The affected area is the leg, close-up view, the subject is female: 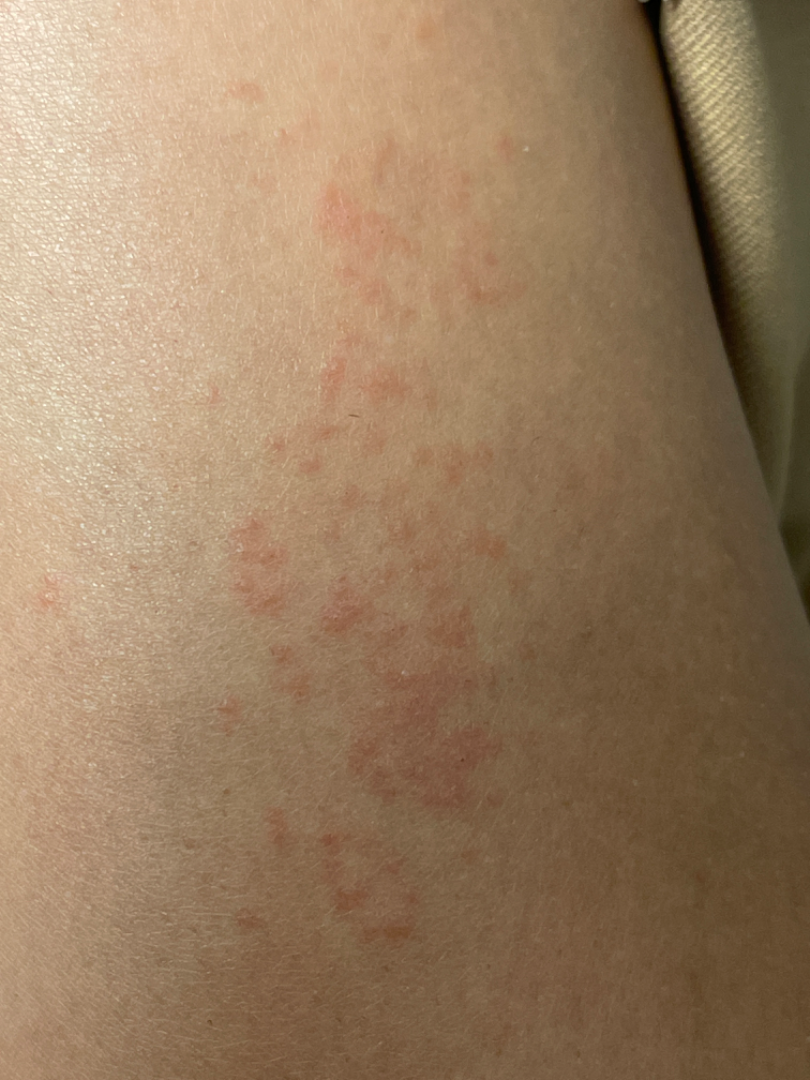impression: Eczema and Allergic Contact Dermatitis were each considered, in no particular order